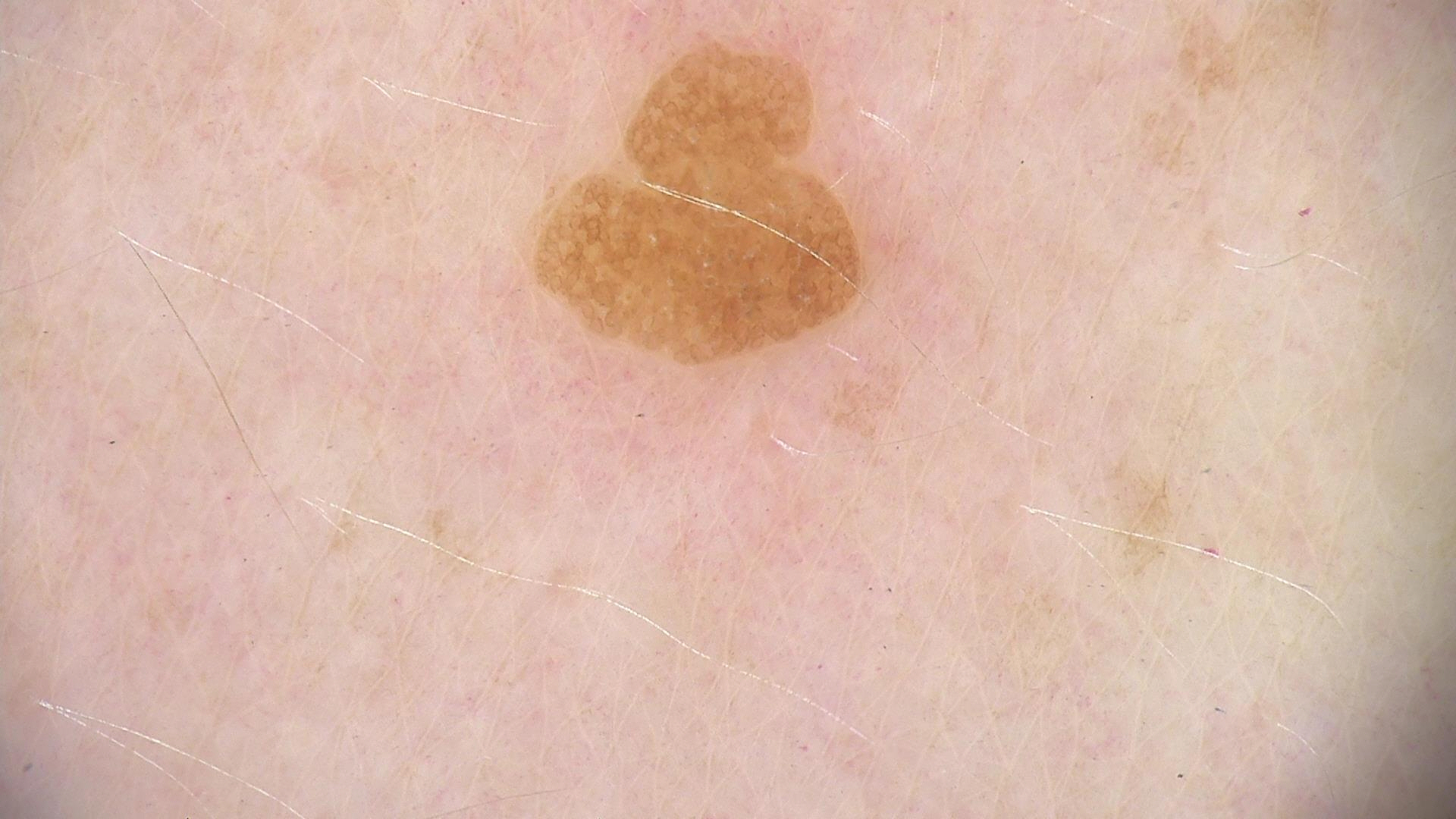Findings: A dermoscopic close-up of a skin lesion. Conclusion: The diagnosis was a keratinocytic lesion — a seborrheic keratosis.